Close-up view · Fitzpatrick skin type II; lay graders estimated a Monk Skin Tone of 1 — 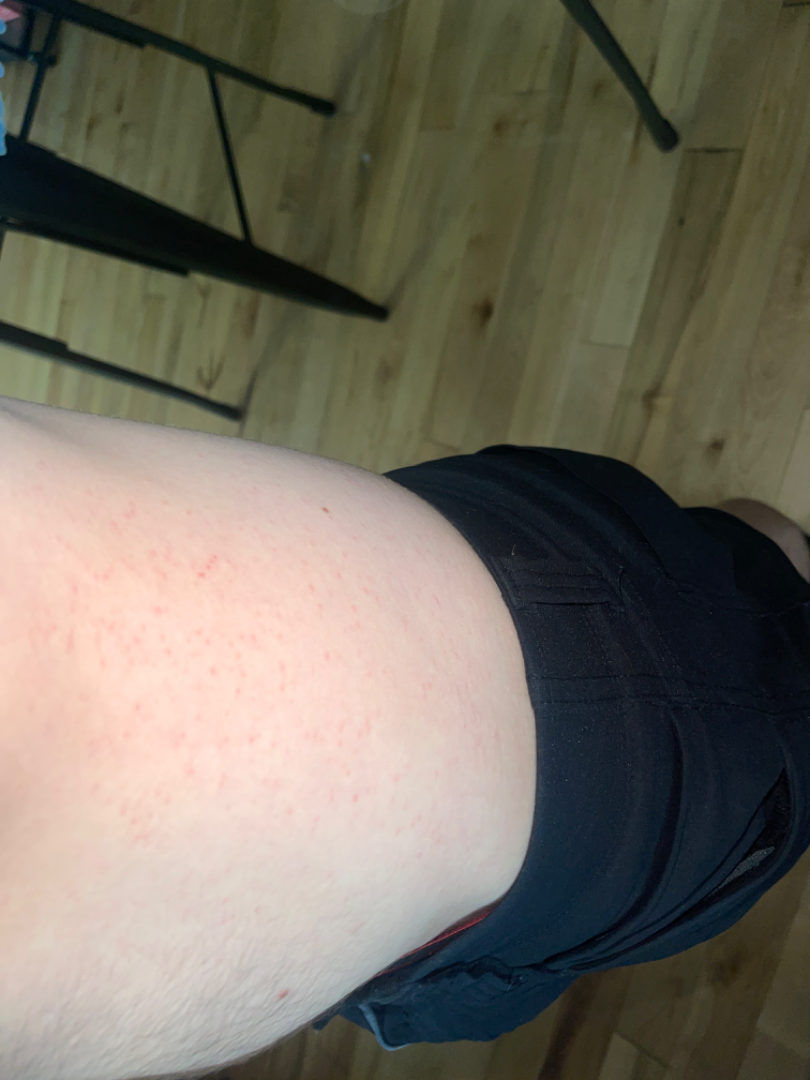One reviewing dermatologist: the favored diagnosis is Keratosis pilaris; also raised was Folliculitis; less likely is Eczema.